A close-up photograph, the affected area is the leg, the subject is a female aged 60–69:
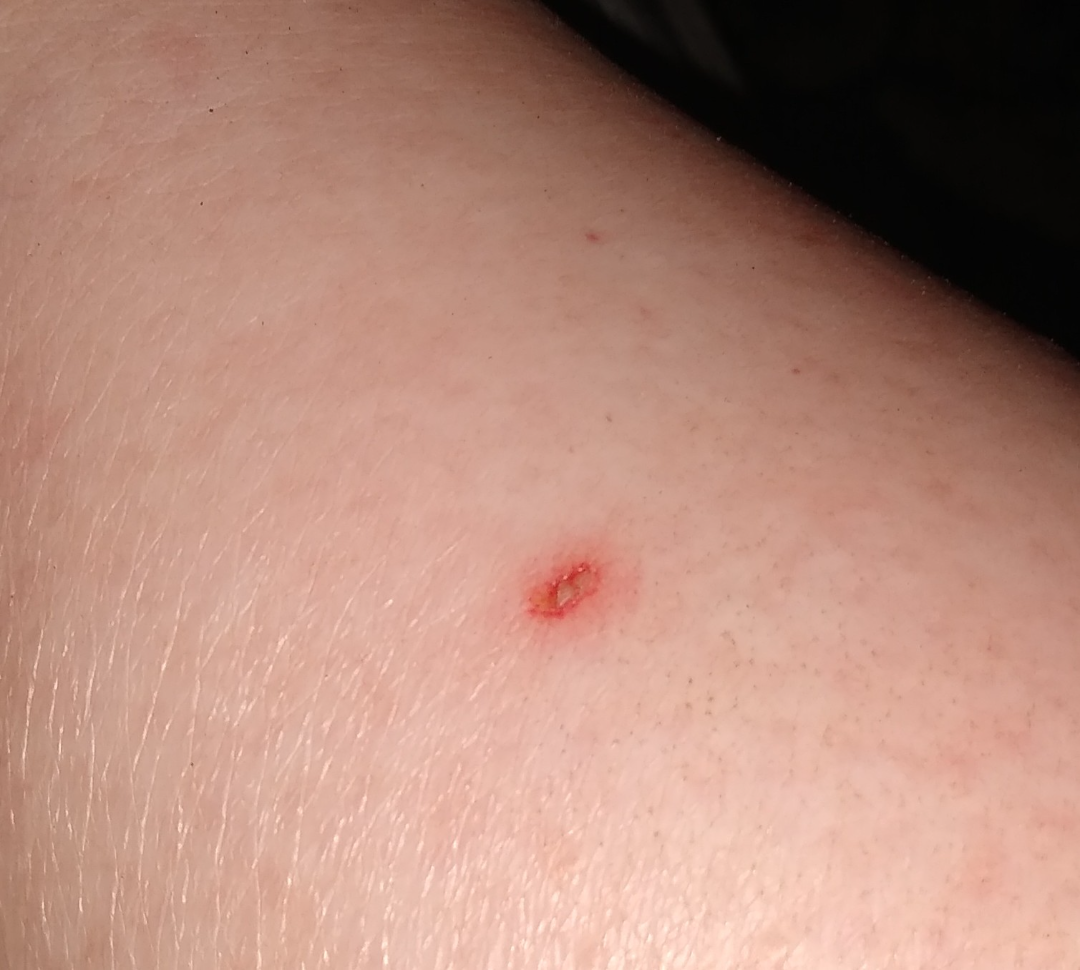On dermatologist assessment of the image, Insect Bite (favored); Impetigo (considered); Folliculitis (less likely); Viral infection of skin (less likely); Allergic Contact Dermatitis (less likely).